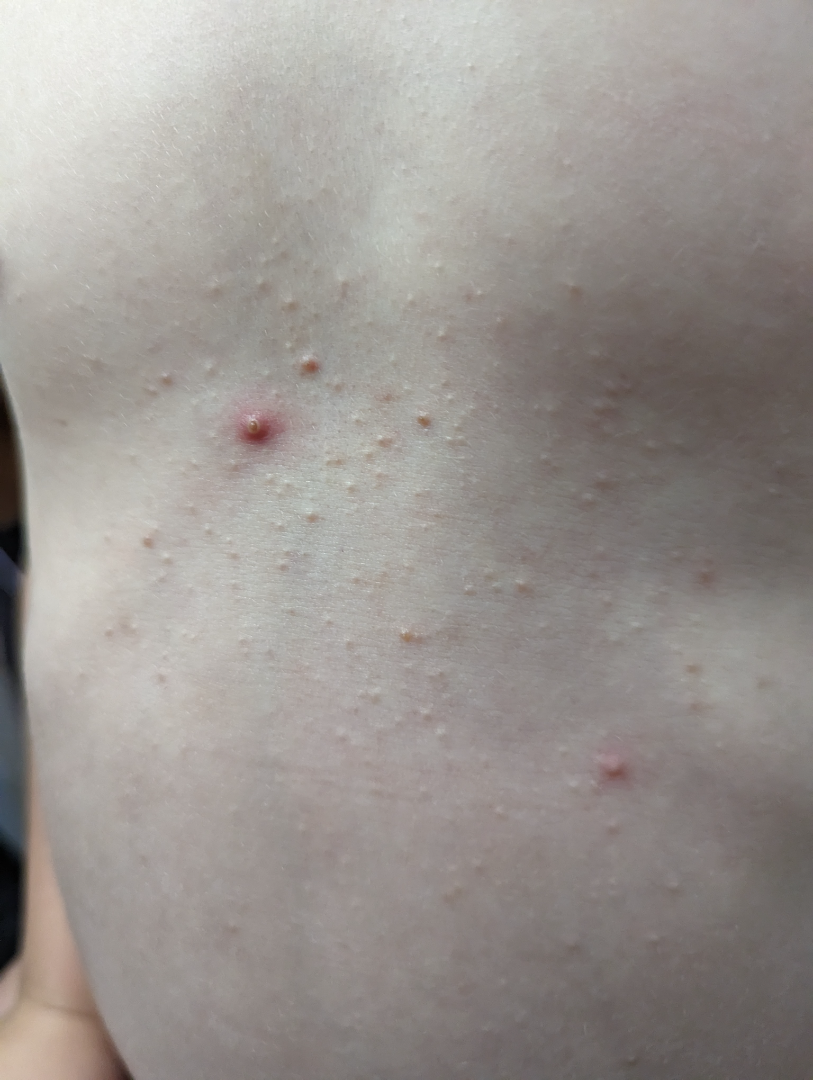Findings:
- texture: raised or bumpy and fluid-filled
- symptom duration: more than one year
- anatomic site: front of the torso
- skin tone: FST II
- image framing: close-up